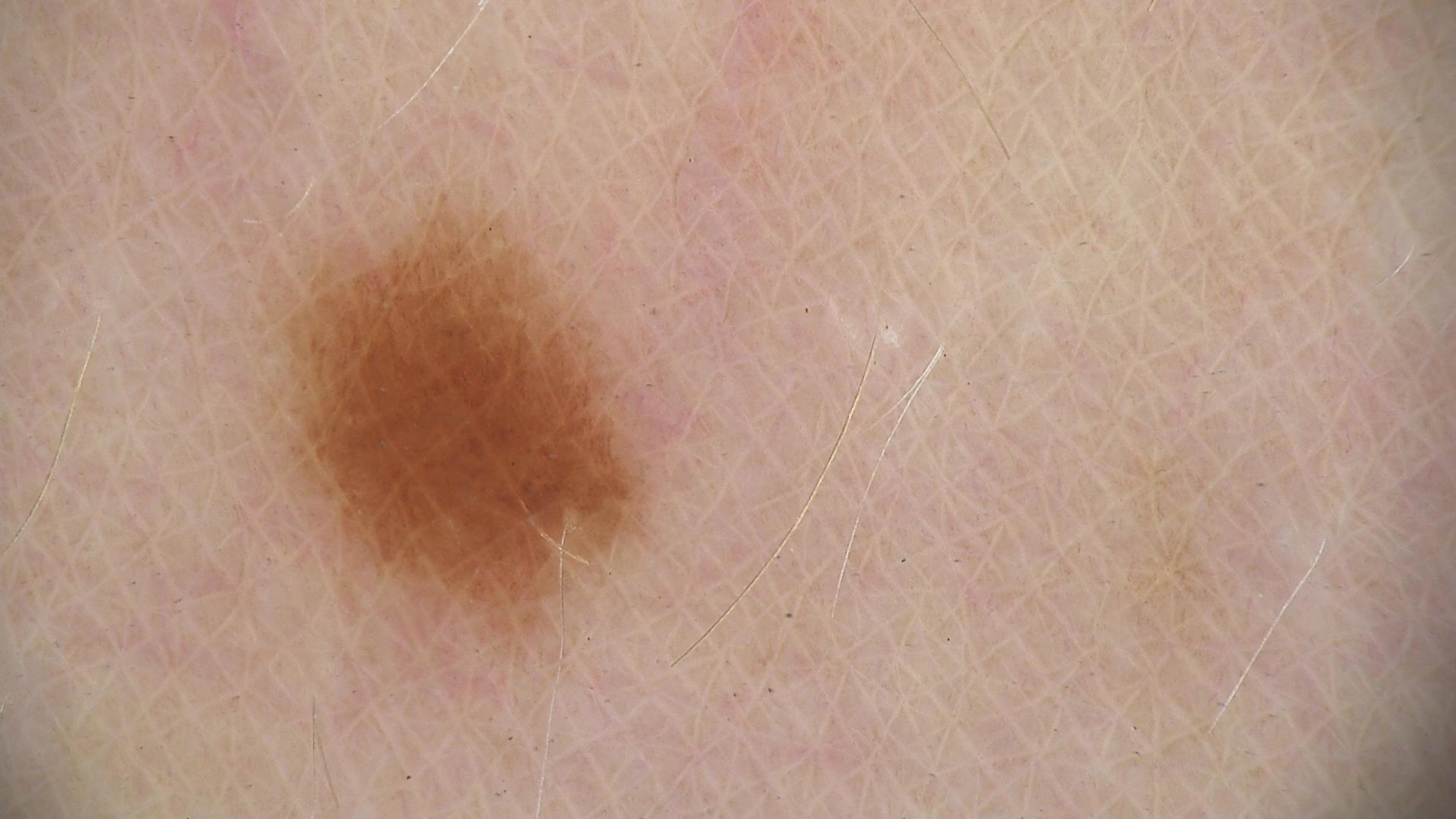A dermatoscopic image of a skin lesion. Classified as a banal lesion — a junctional nevus.